Female patient, age 50–59 · the patient considered this a rash · the patient reports the condition has been present for three to twelve months · the lesion involves the leg · the patient reports darkening, burning, bothersome appearance, itching and pain · an image taken at a distance:
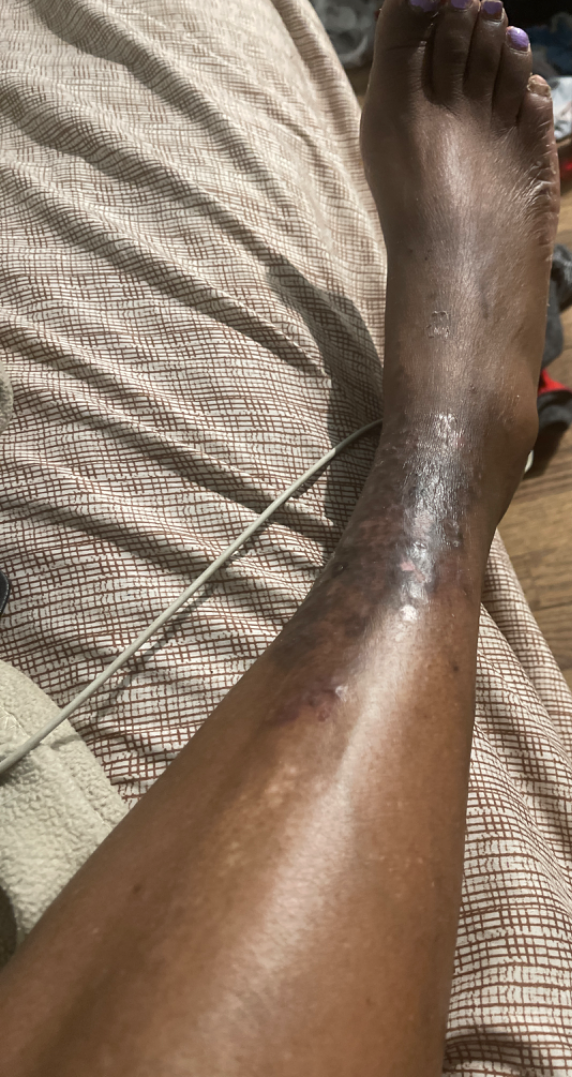diagnostic considerations: Eczema (primary); Stasis Dermatitis (considered); Lichen Simplex Chronicus (unlikely); Lichen planus/lichenoid eruption (unlikely)